The photo was captured at an angle, the affected area is the arm.
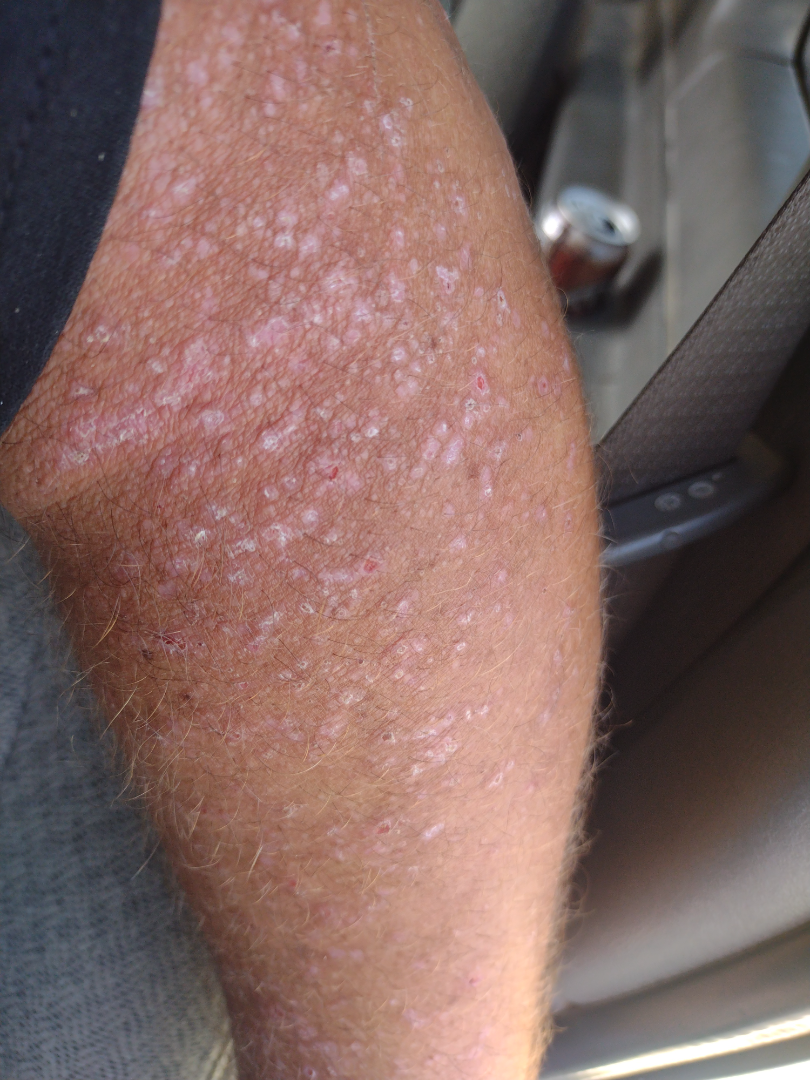Impression: Favoring Psoriasis; also on the differential is Drug Rash.